A dermoscopic photograph of a skin lesion; skin type III — 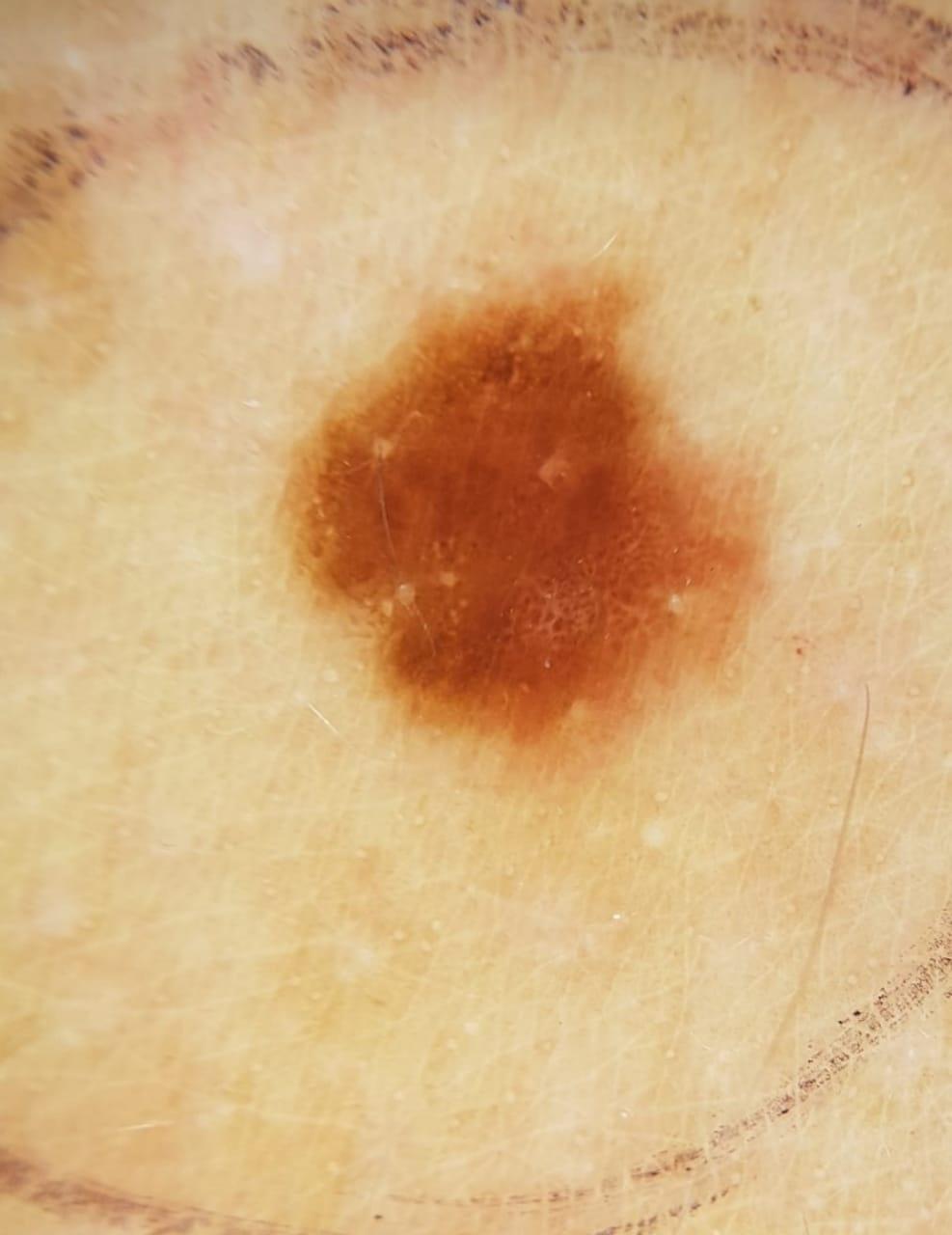diagnosis=Nevus (biopsy-proven).